The condition has been present for one to four weeks · the patient described the issue as a rash · the photograph was taken at a distance · the patient is female · the affected area is the arm:
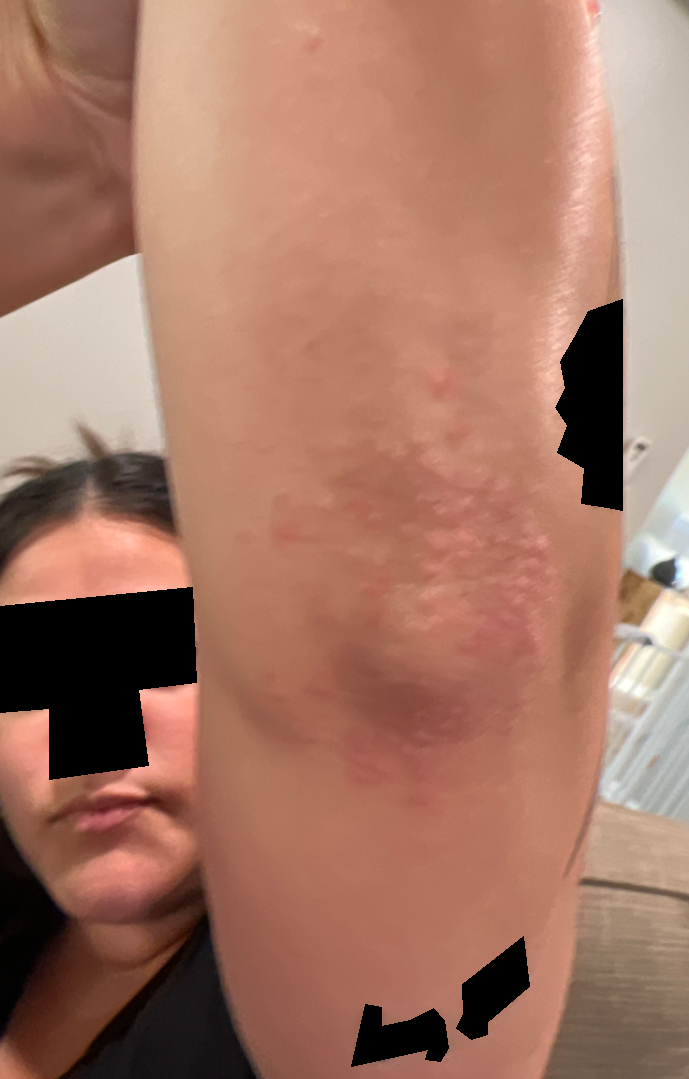Eczema (possible); Lichen Simplex Chronicus (possible); Psoriasis (less likely); Perforating dermatosis (less likely); Granuloma annulare (less likely); Dermatitis herpetiformis (less likely).